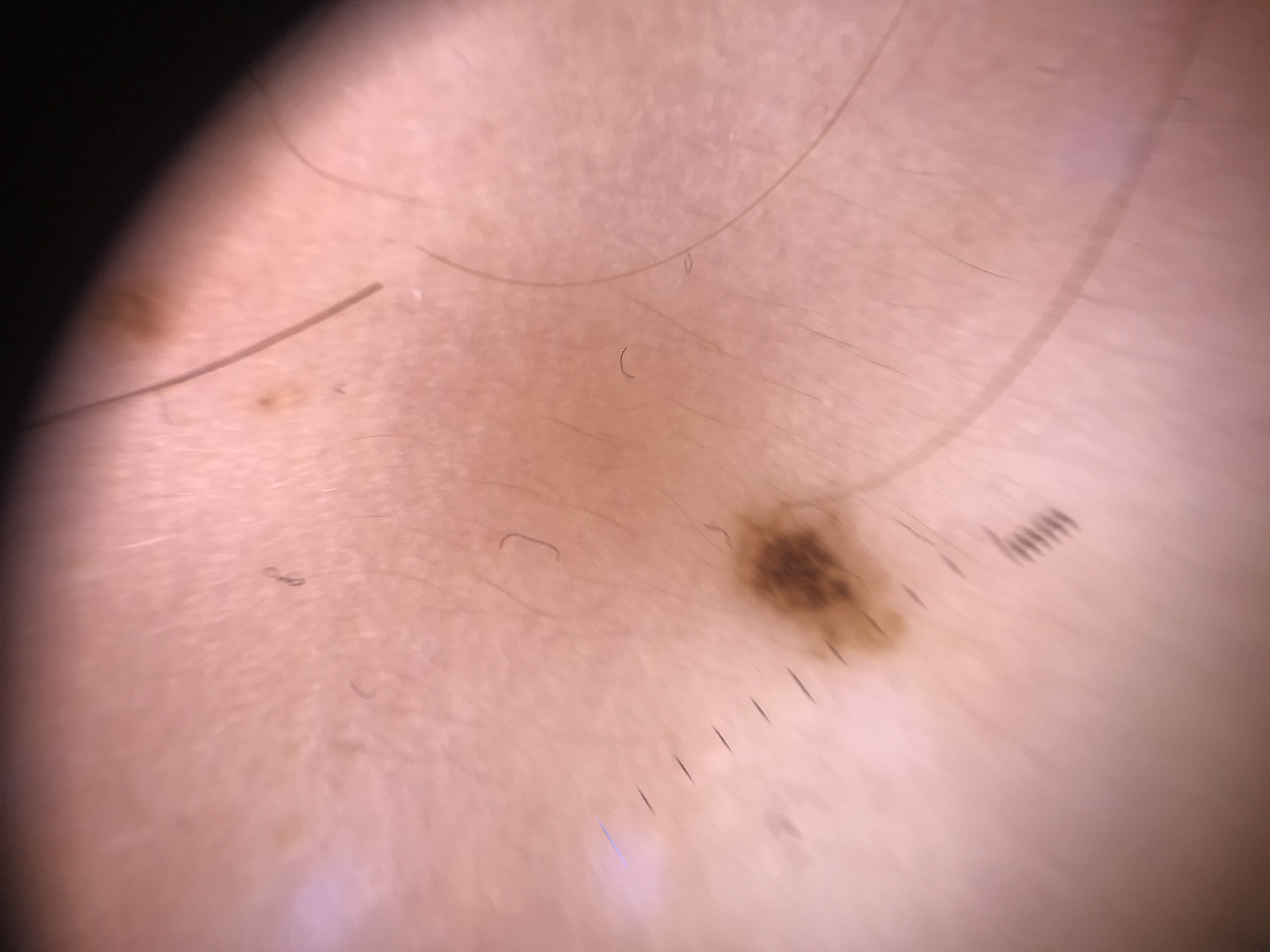* image · dermatoscopy
* subtype · banal
* diagnostic label · junctional nevus (expert consensus)